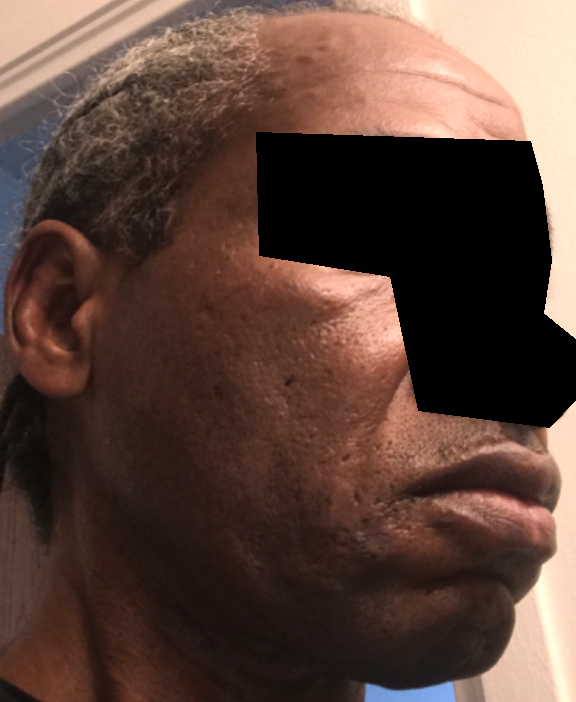The impression was split between Post-Inflammatory hyperpigmentation and Scar Condition.